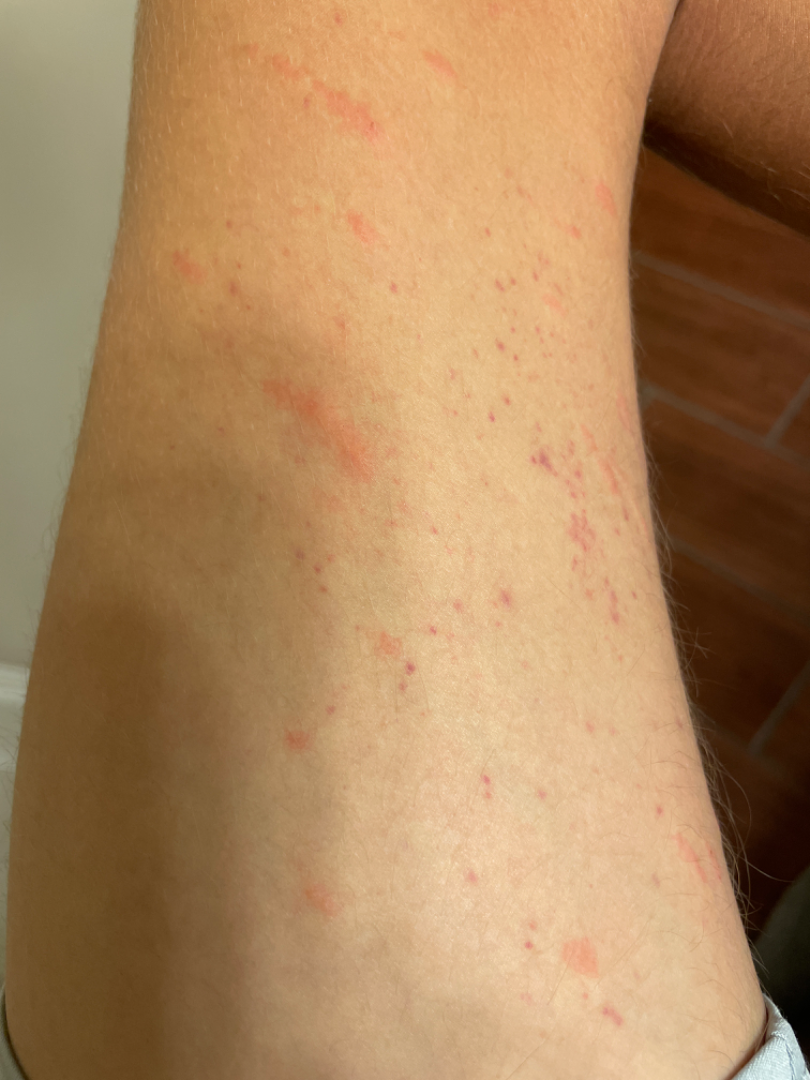assessment: could not be assessed